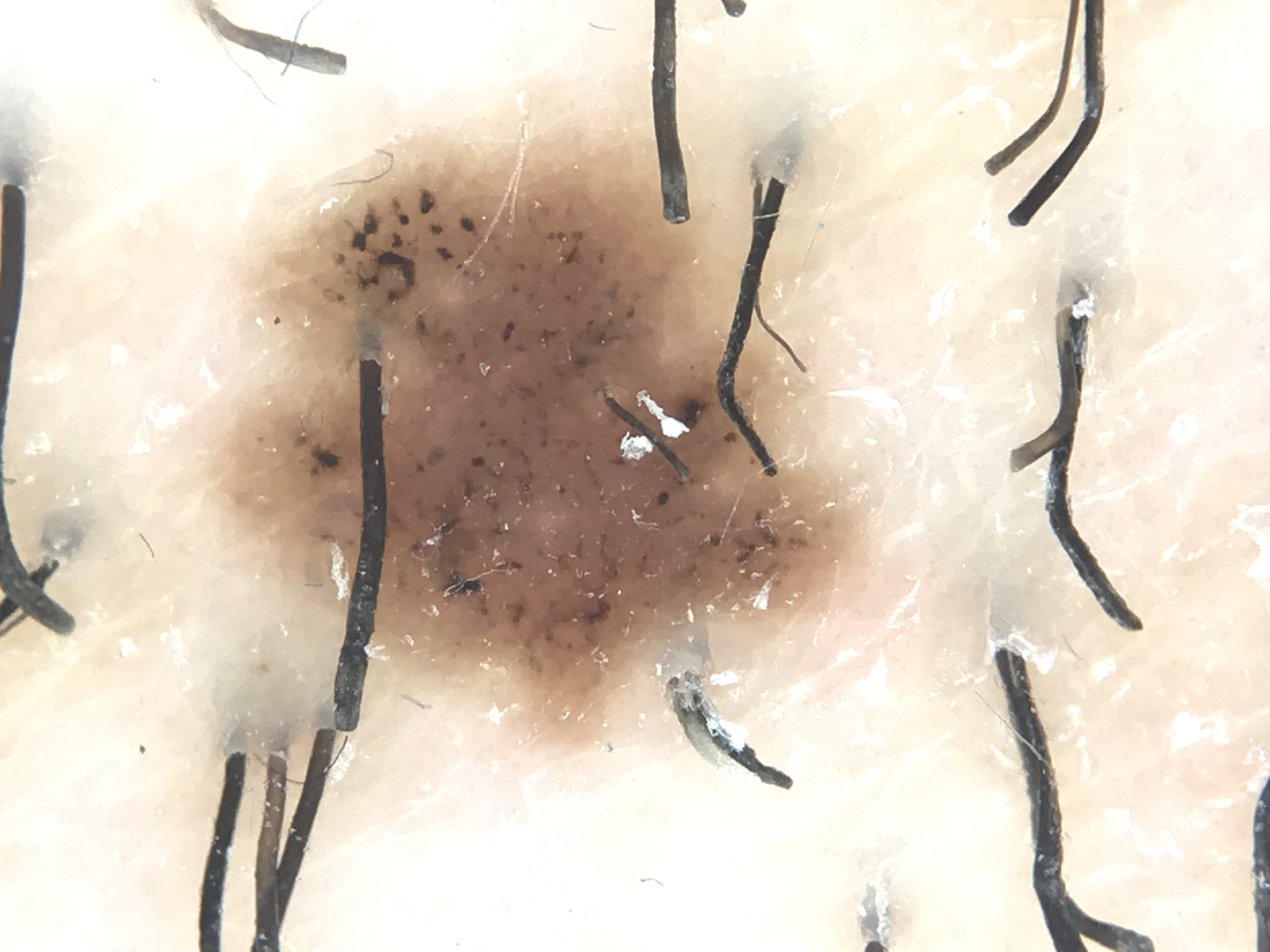Q: What kind of image is this?
A: dermoscopy
Q: What is this lesion?
A: compound nevus (expert consensus)